A dermoscopy image of a single skin lesion:
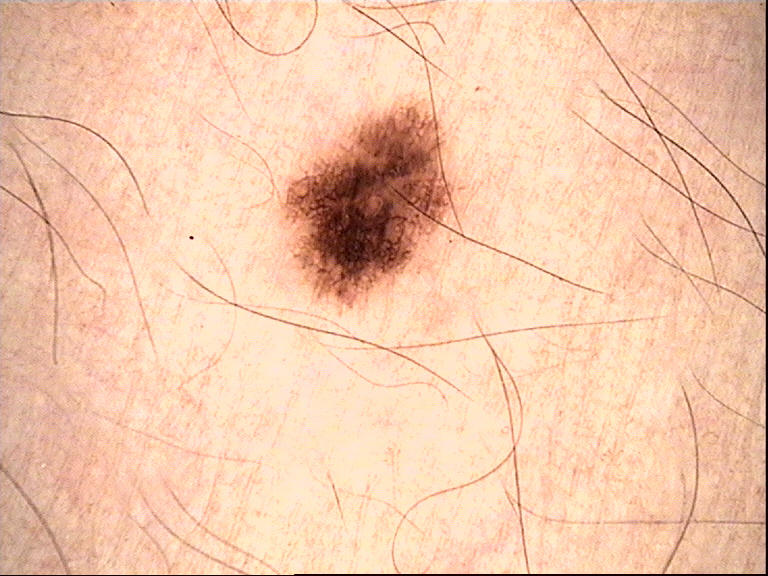Diagnosed as a dysplastic junctional nevus.